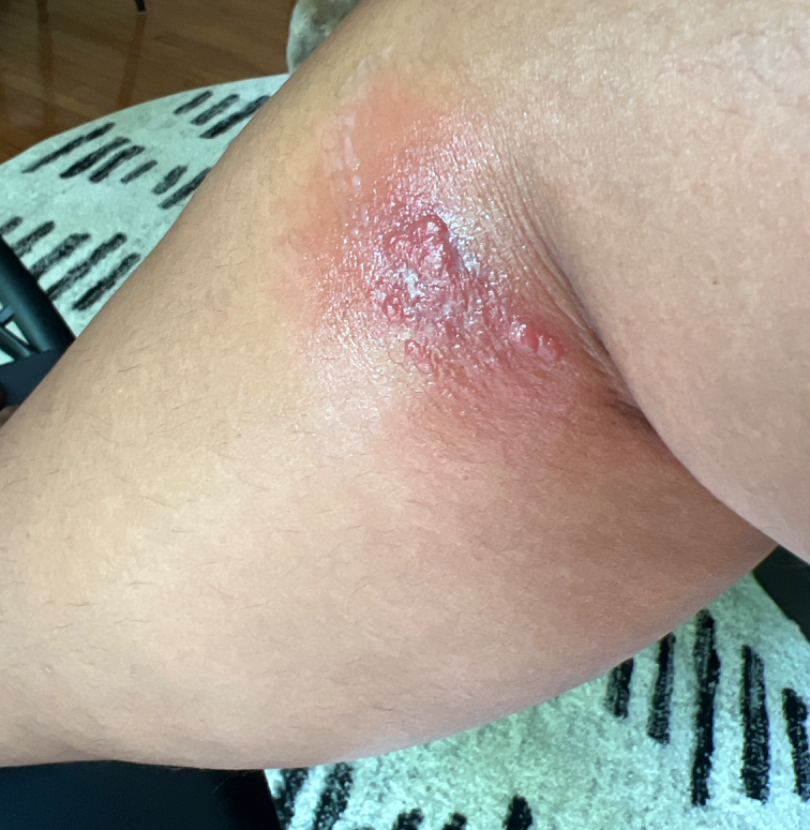Q: How does the patient describe it?
A: skin that appeared healthy to them
Q: How does the lesion feel?
A: raised or bumpy
Q: How was the photo taken?
A: at an angle
Q: What is the patient's skin tone?
A: Fitzpatrick III; lay reviewers estimated Monk skin tone scale 6 (US pool) or 4 (India pool)
Q: Constitutional symptoms?
A: none reported
Q: Anatomic location?
A: leg
Q: Who is the patient?
A: female, age 30–39
Q: Reported symptoms?
A: pain
Q: What is the differential diagnosis?
A: most consistent with Cellulitis; with consideration of Contact dermatitis; lower on the differential is Infected eczema; less probable is Molluscum Contagiosum